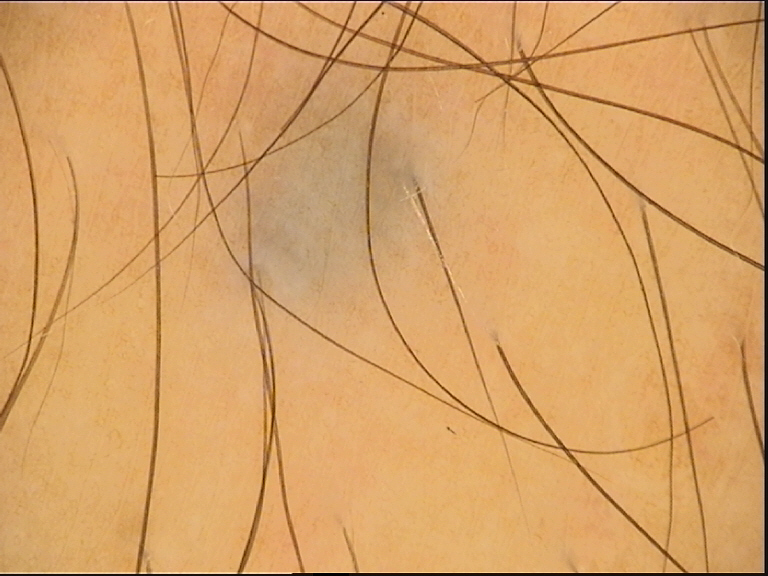diagnosis: blue nevus (expert consensus).